Female contributor, age 50–59. Skin tone: lay graders estimated a MST of 4. The patient described the issue as a rash. Reported lesion symptoms include itching and enlargement. A close-up photograph. The lesion involves the arm. The lesion is described as raised or bumpy. Reported duration is one to four weeks: 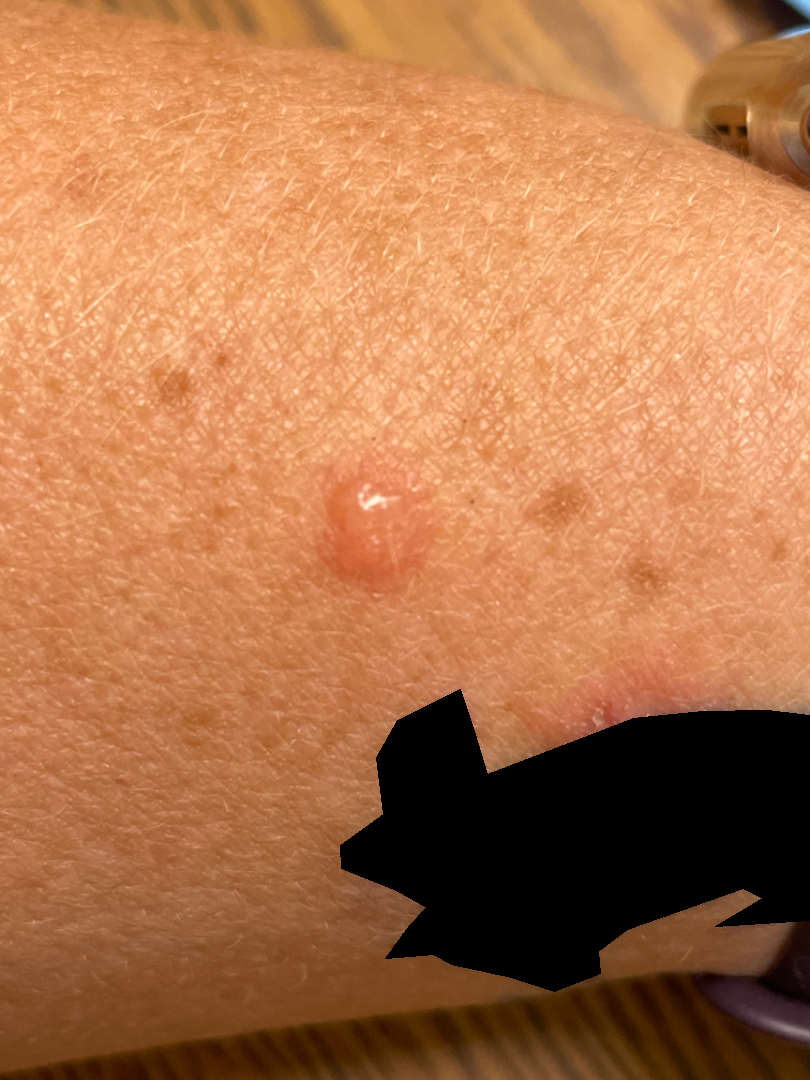Findings:
- assessment — indeterminate from the photograph